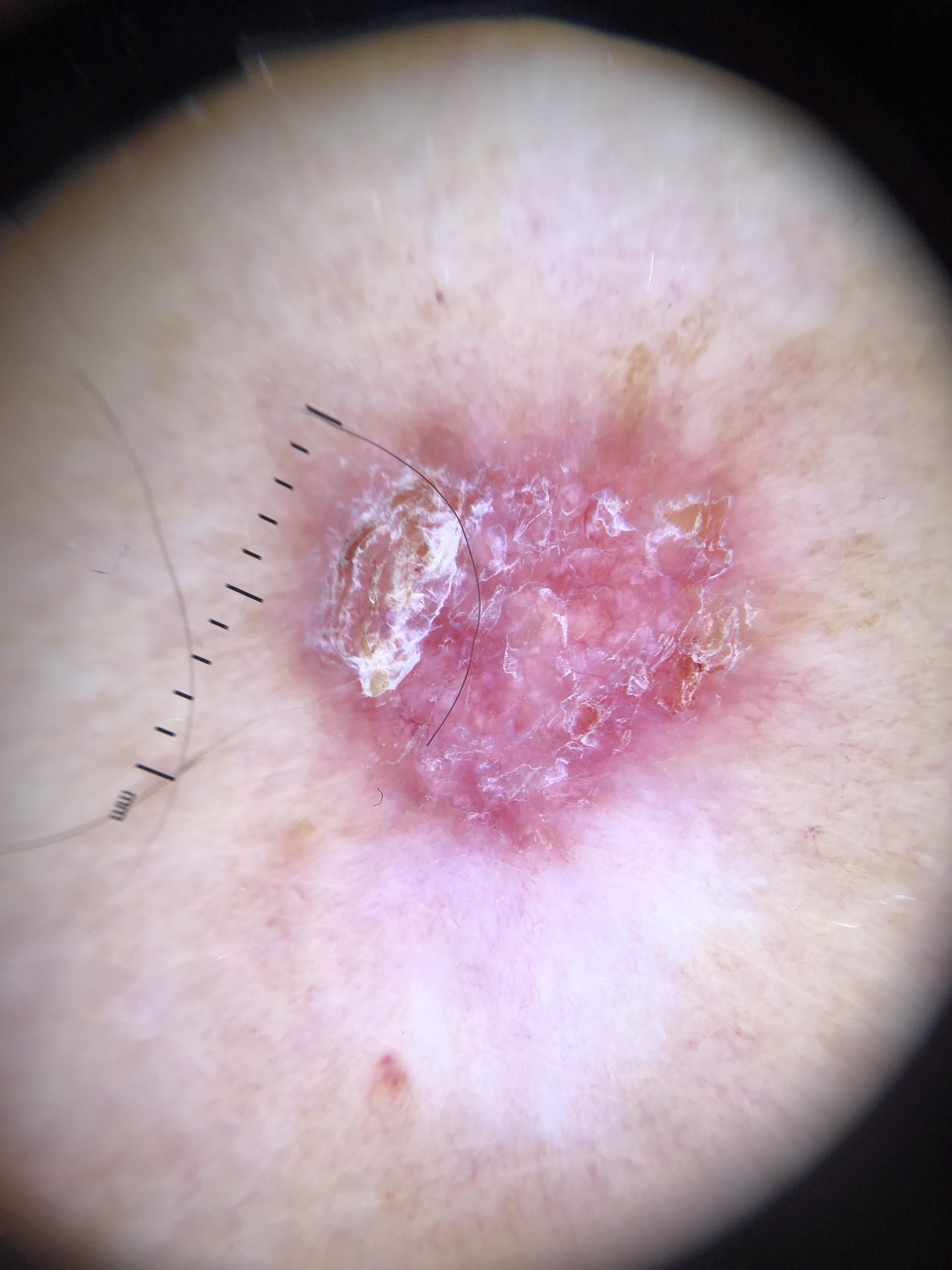A male subject about 80 years old. The lesion was found on the posterior trunk. Confirmed on histopathology as a squamous cell carcinoma.